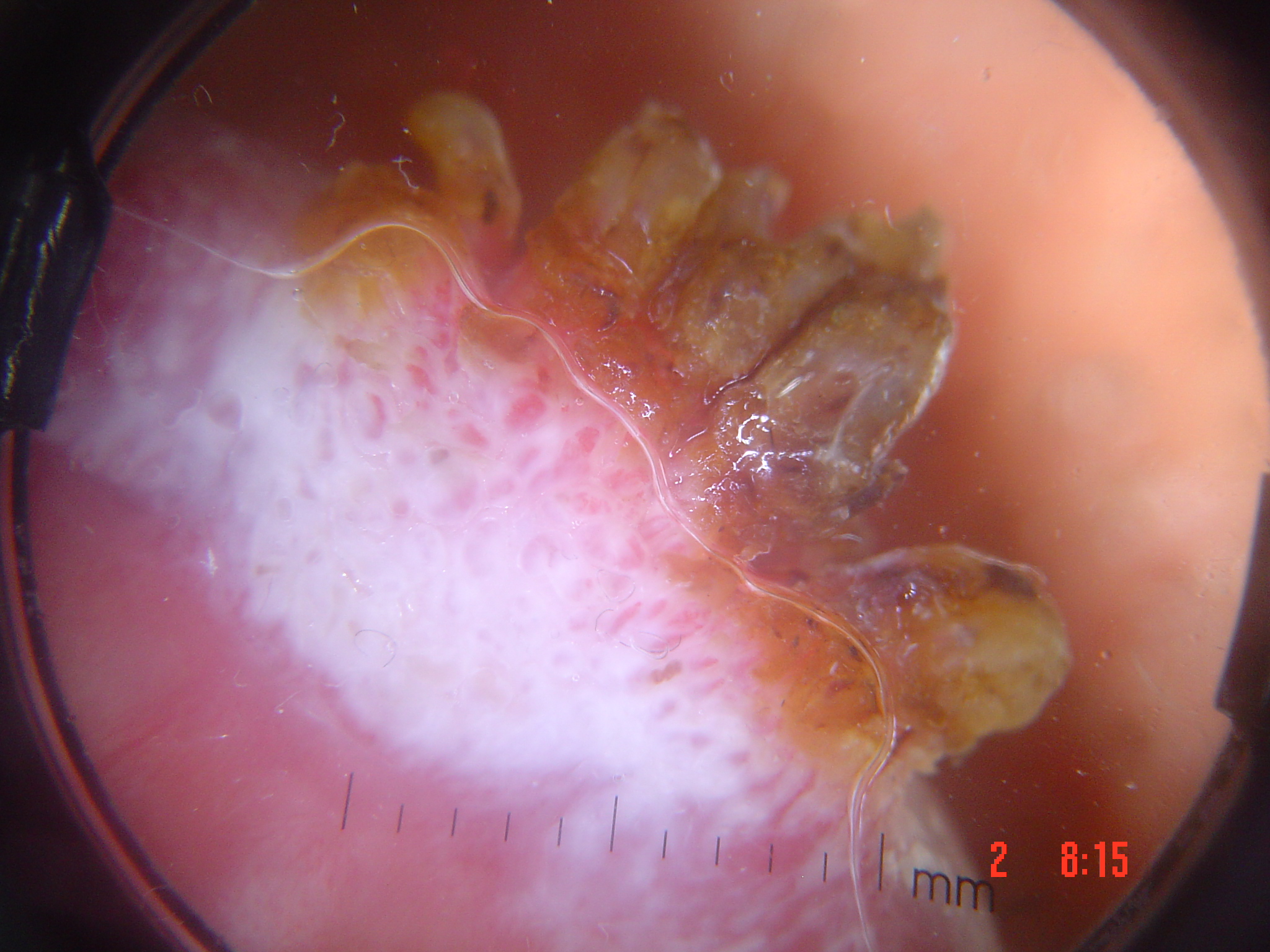diagnostic label: squamous cell carcinoma (biopsy-proven).